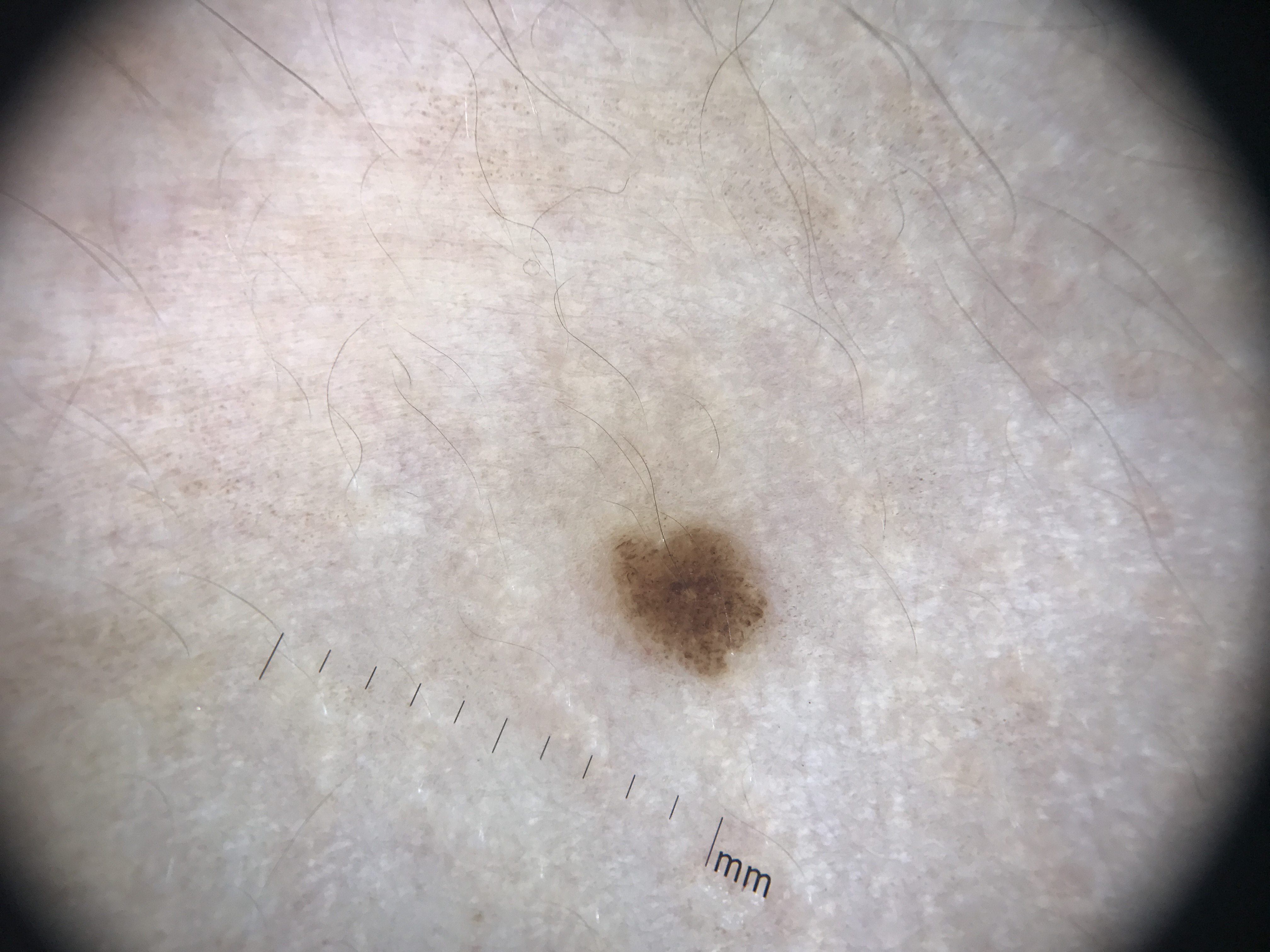  image: dermoscopy
  diagnosis:
    name: dysplastic junctional nevus
    code: jd
    malignancy: benign
    super_class: melanocytic
    confirmation: expert consensus